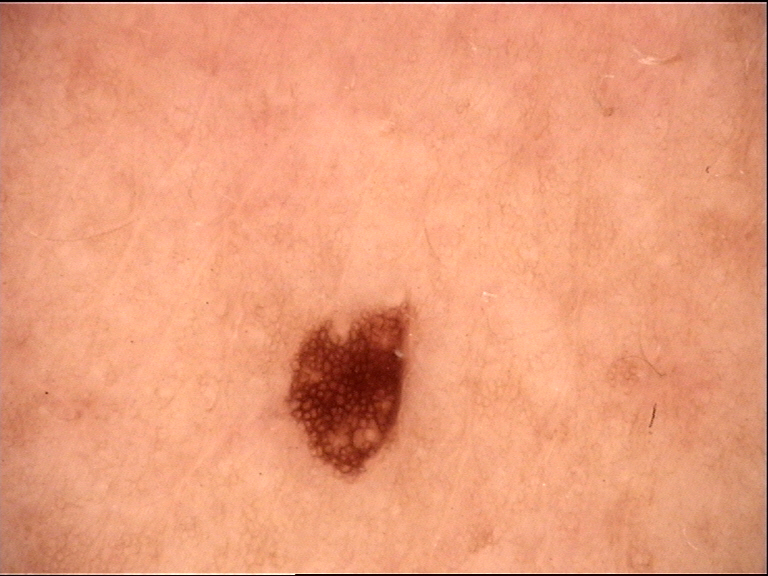Diagnosed as a dysplastic junctional nevus.